A dermoscopic photograph of a skin lesion: 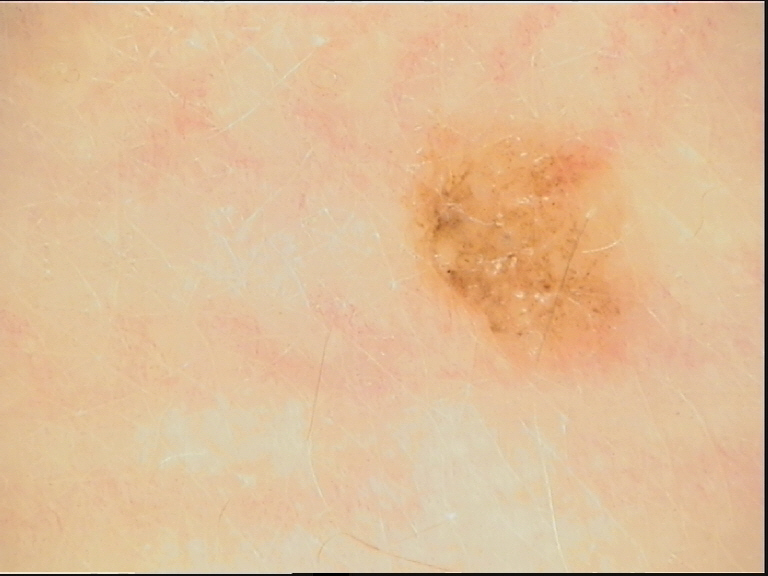Conclusion:
Classified as a dysplastic junctional nevus.